A female patient, aged 53 to 57. A dermoscopic view of a skin lesion.
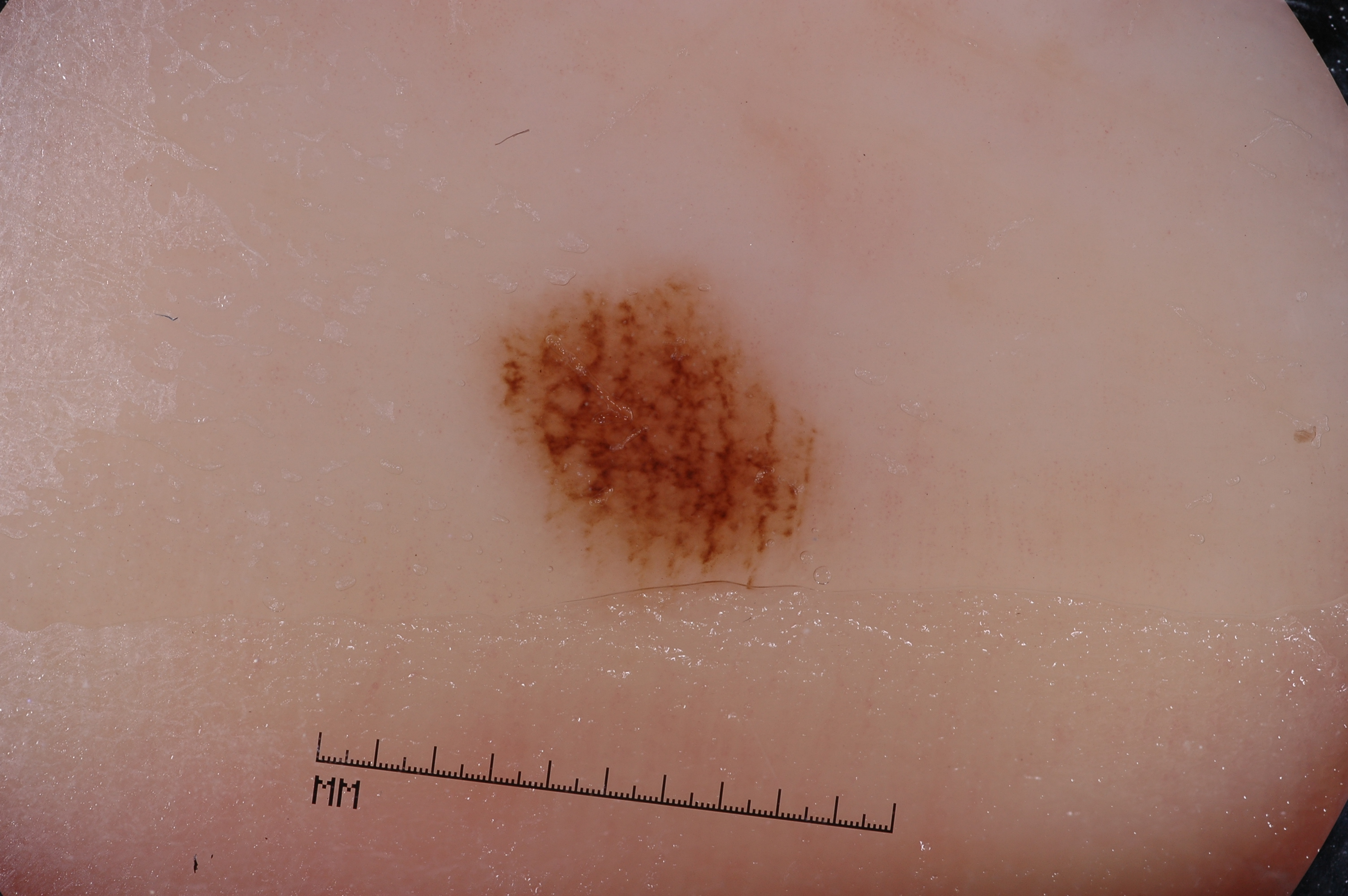The lesion is bounded by box(490, 272, 834, 616). On dermoscopy, the lesion shows no streaks, negative network, pigment network, or milia-like cysts. The clinical diagnosis was a melanocytic nevus, a benign lesion.